A skin lesion imaged with a dermatoscope. A male patient 58 years of age. Numerous moles by the patient's own estimate. The patient says their skin tans without first burning — 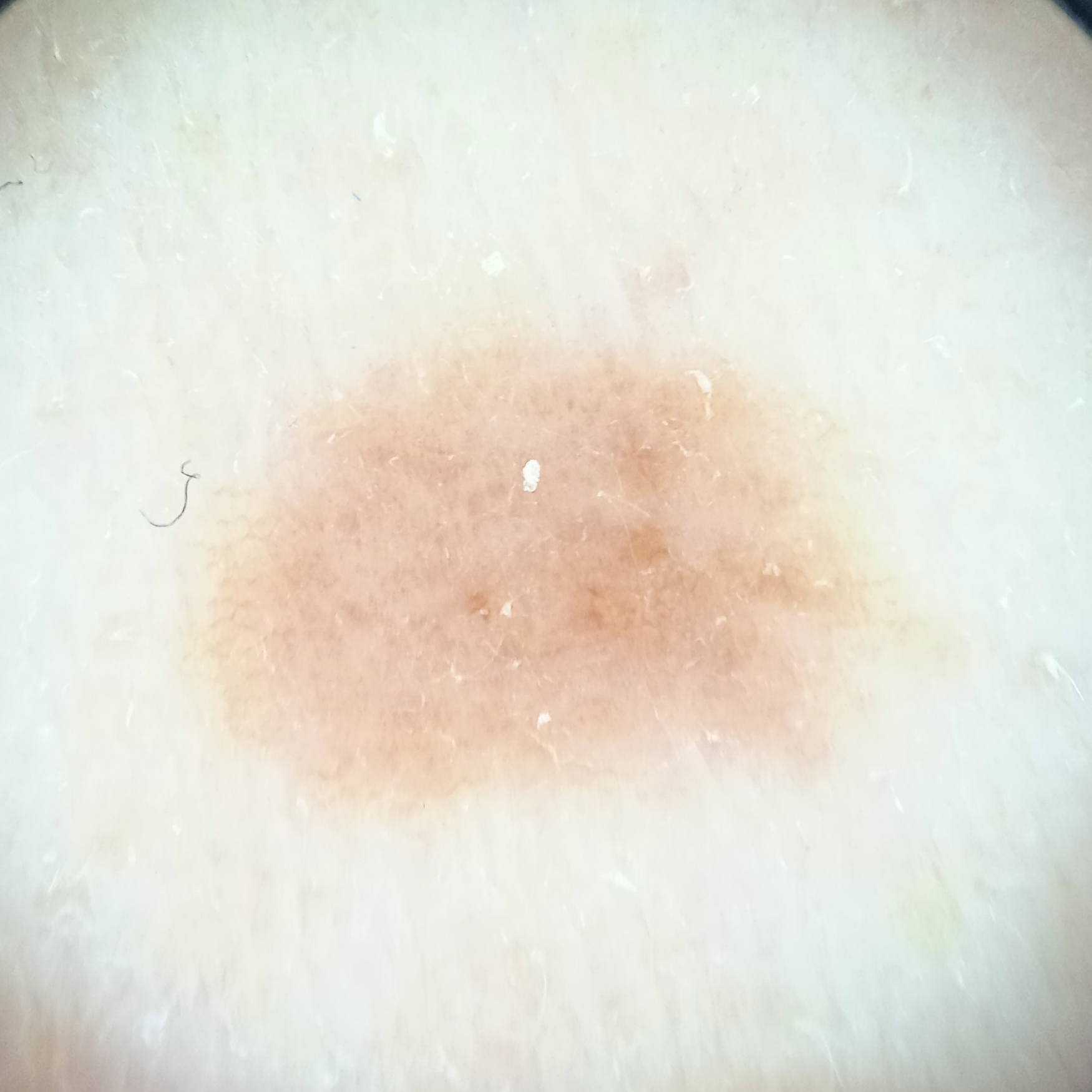Q: Where is the lesion?
A: the back
Q: Lesion size?
A: 8.6 mm
Q: What was the diagnosis?
A: atypical (dysplastic) nevus — dermatologist consensus